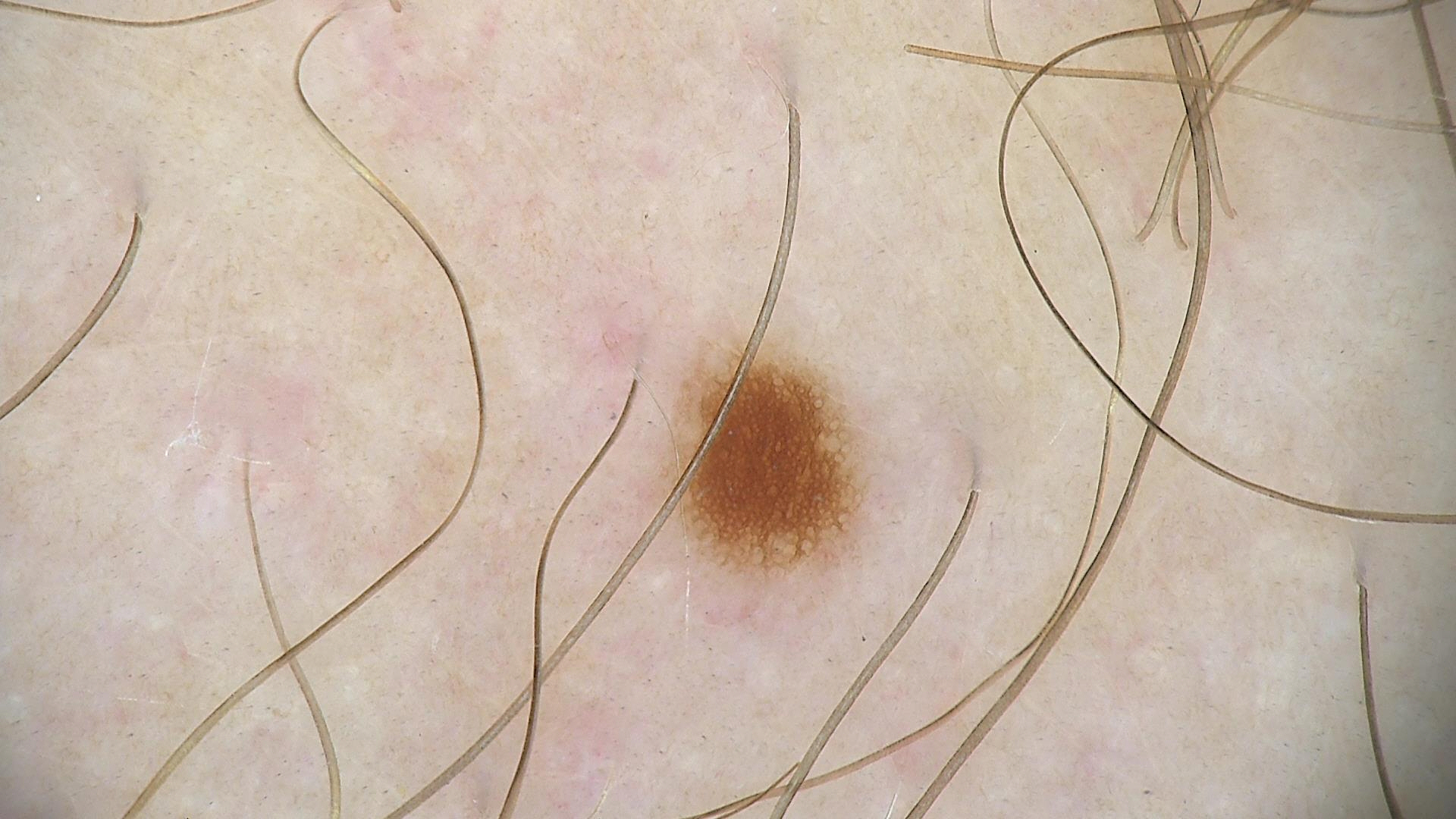Case: A dermoscopy image of a single skin lesion. Conclusion: Consistent with a benign lesion — a dysplastic junctional nevus.